A dermatoscopic image of a skin lesion — 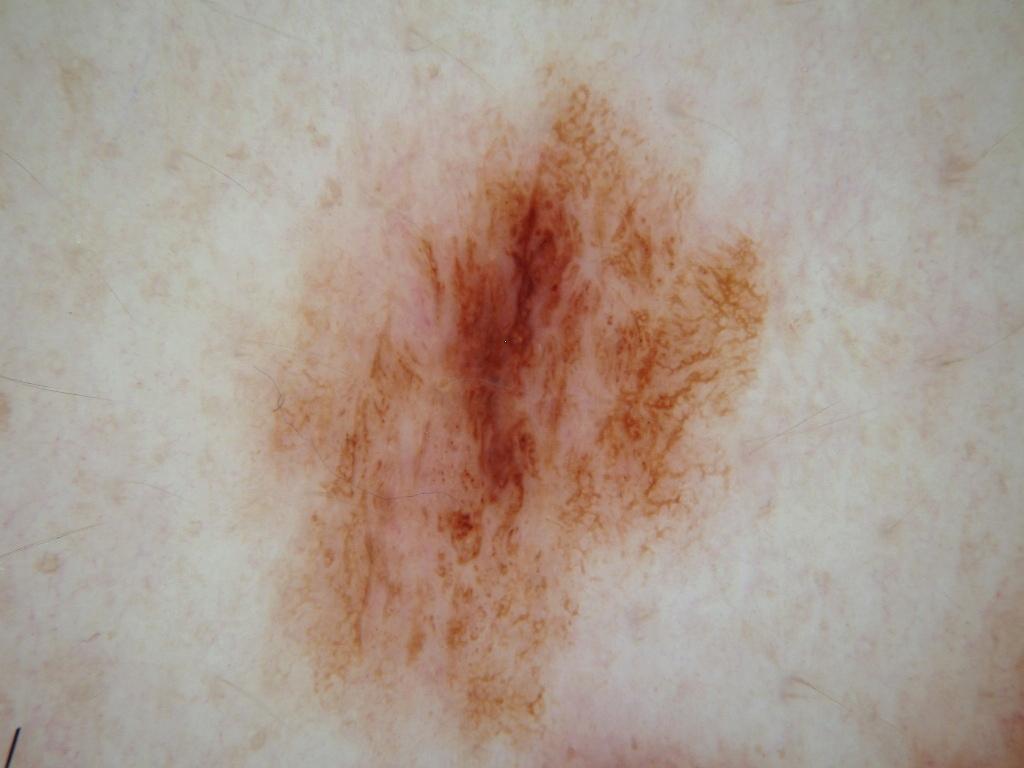features: streaks, globules, and pigment network | bounding box: (224, 50, 794, 763) | lesion size: ~38% of the field | diagnostic label: a melanocytic nevus, a benign lesion.